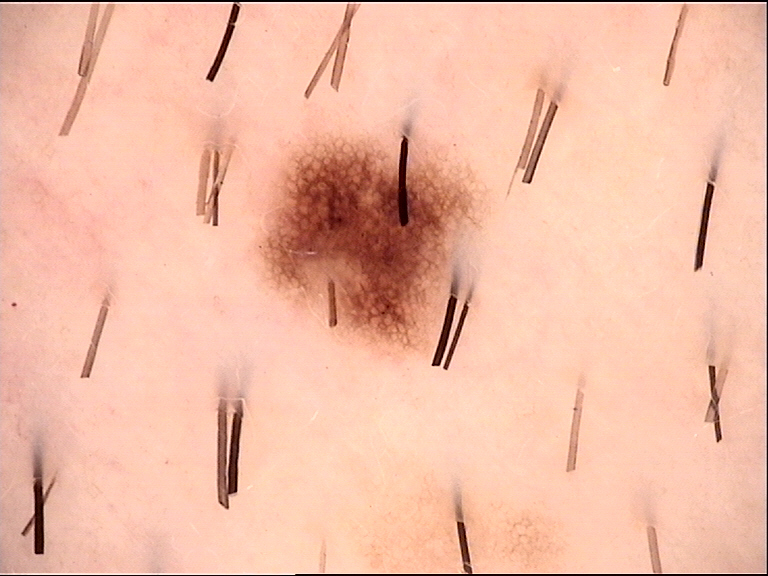modality — dermoscopy | diagnosis — dysplastic junctional nevus (expert consensus).